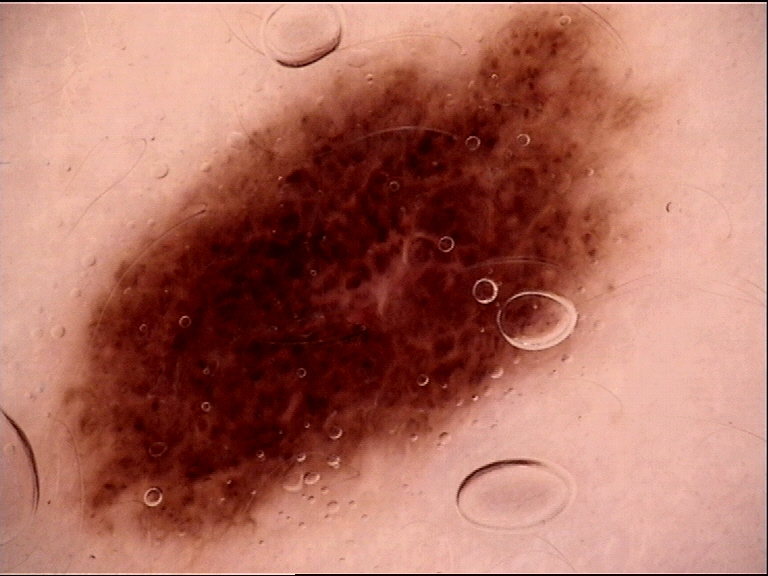Consistent with a dysplastic compound nevus.